This image was taken at an angle:
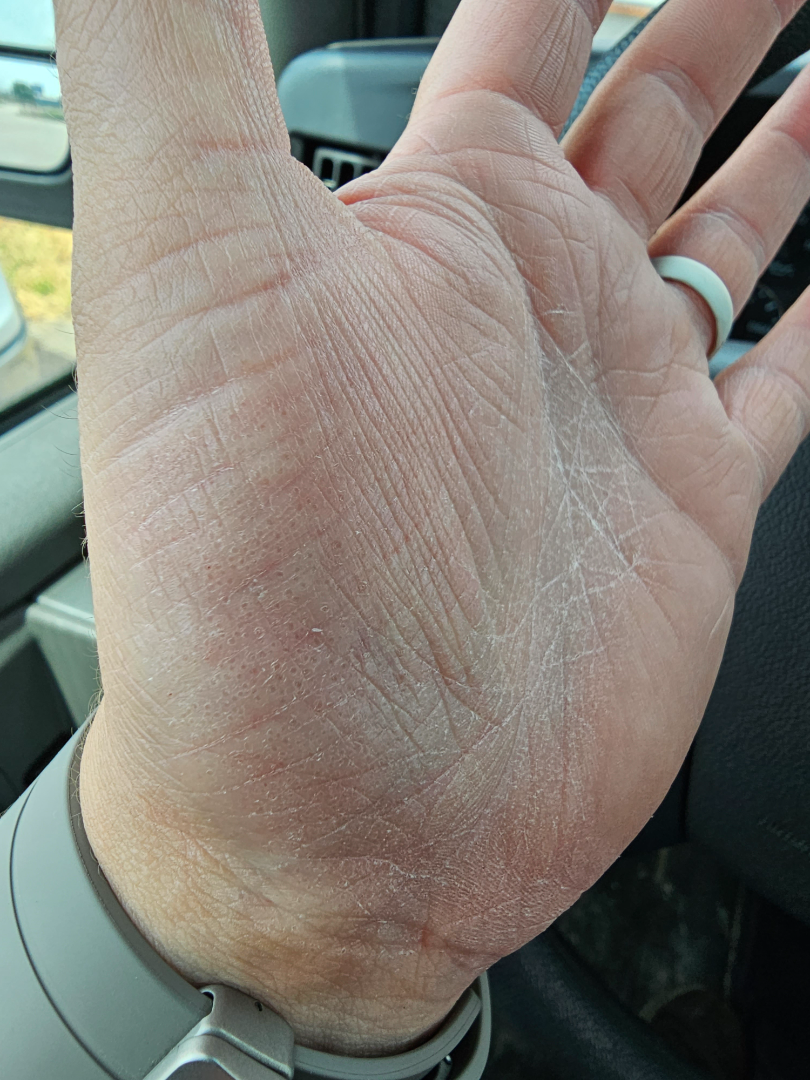clinical impression: Tinea, Eczema and Irritant Contact Dermatitis were each considered, in no particular order.